A dermoscopic photograph of a skin lesion:
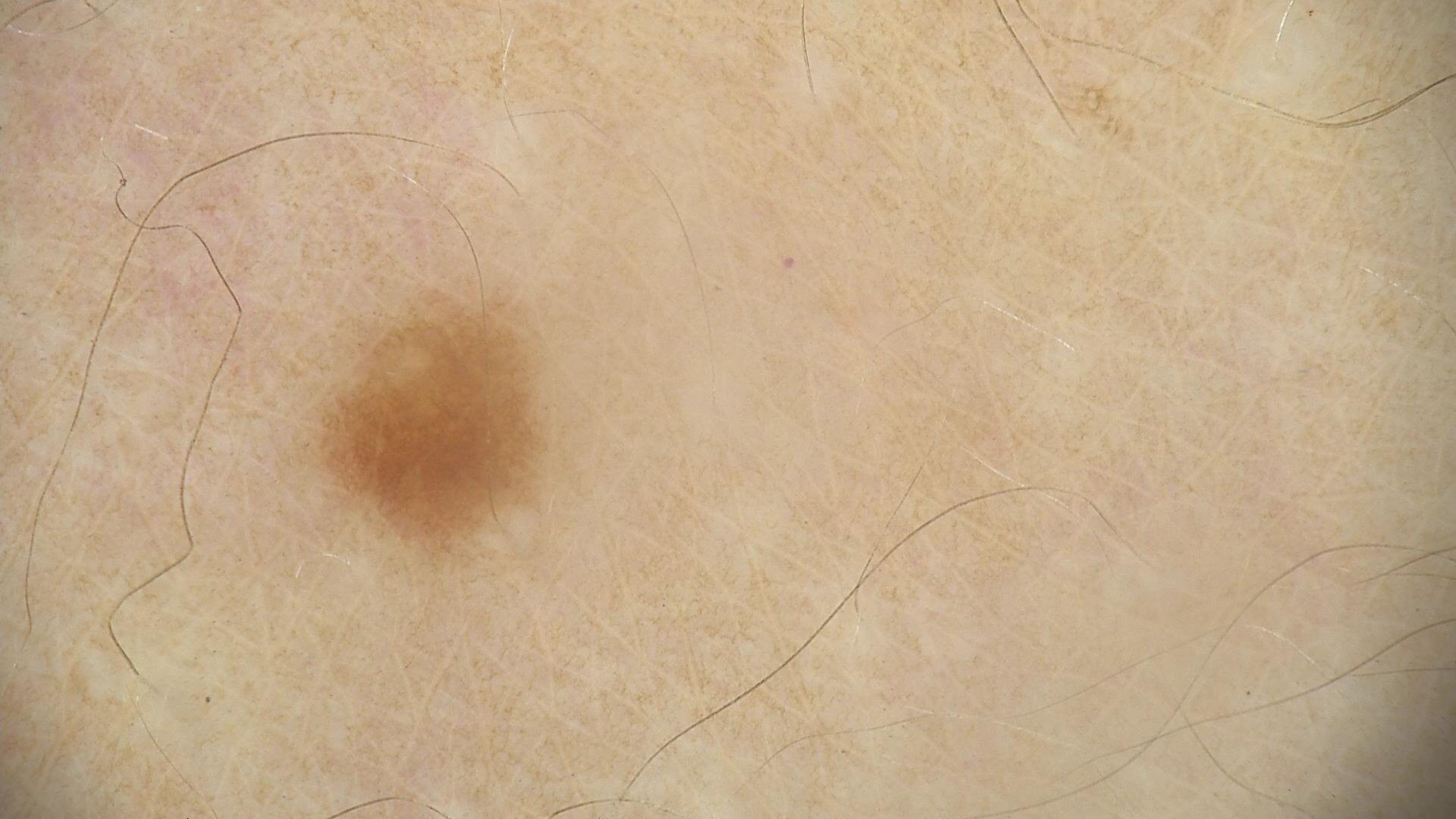assessment = lentigo simplex (expert consensus).